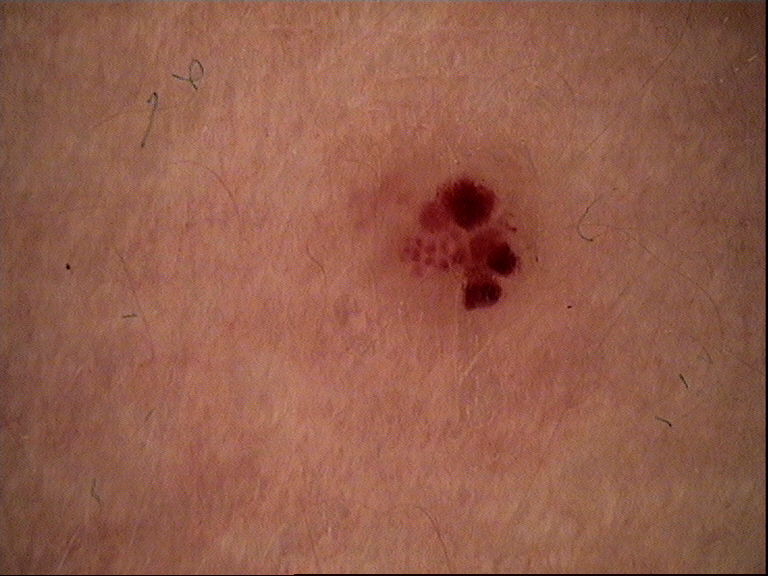Impression: Classified as a hemangioma.